A subject in their 70s. A clinical photo of a skin lesion taken with a smartphone:
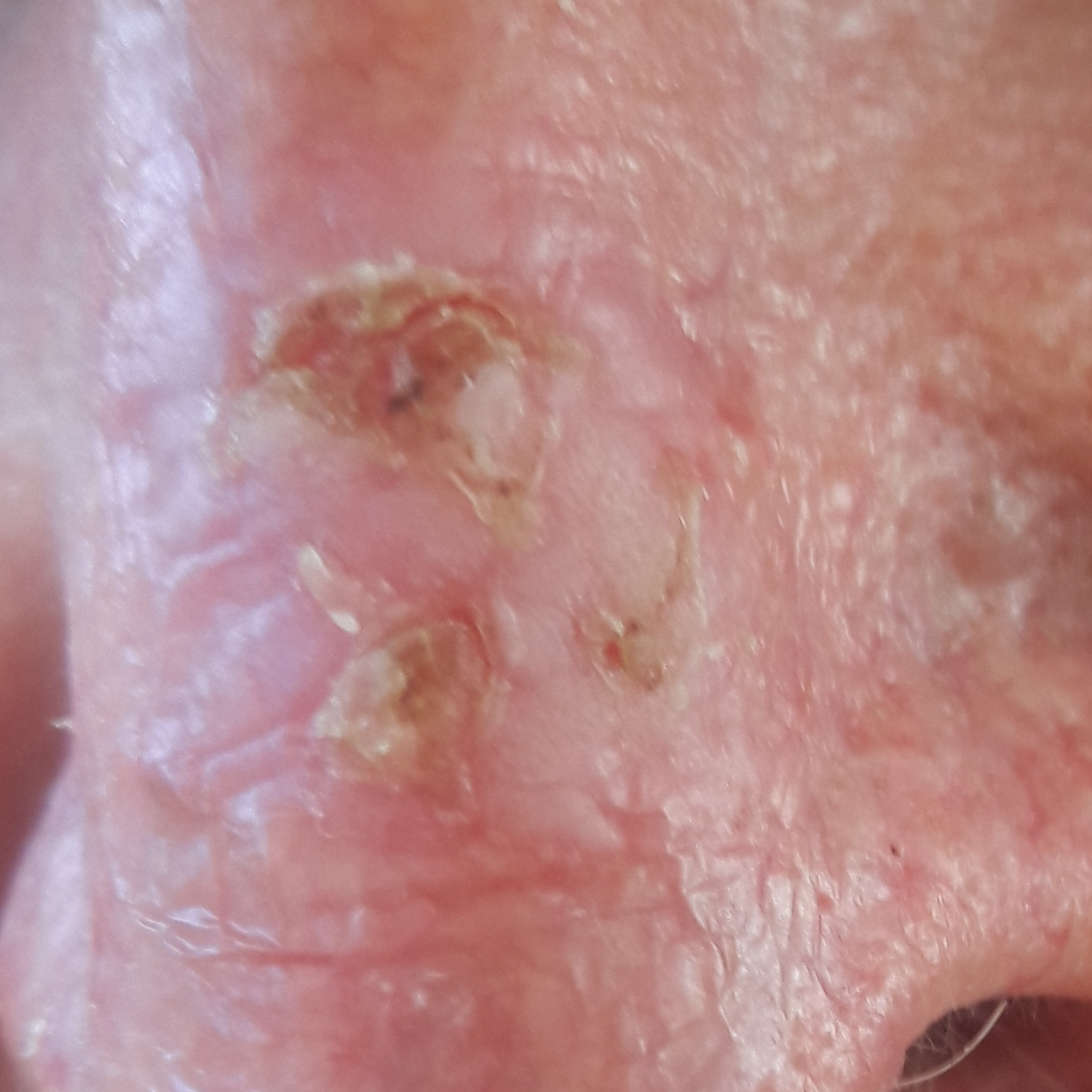| feature | finding |
|---|---|
| reported symptoms | itching, elevation |
| diagnosis | actinic keratosis (clinical consensus) |